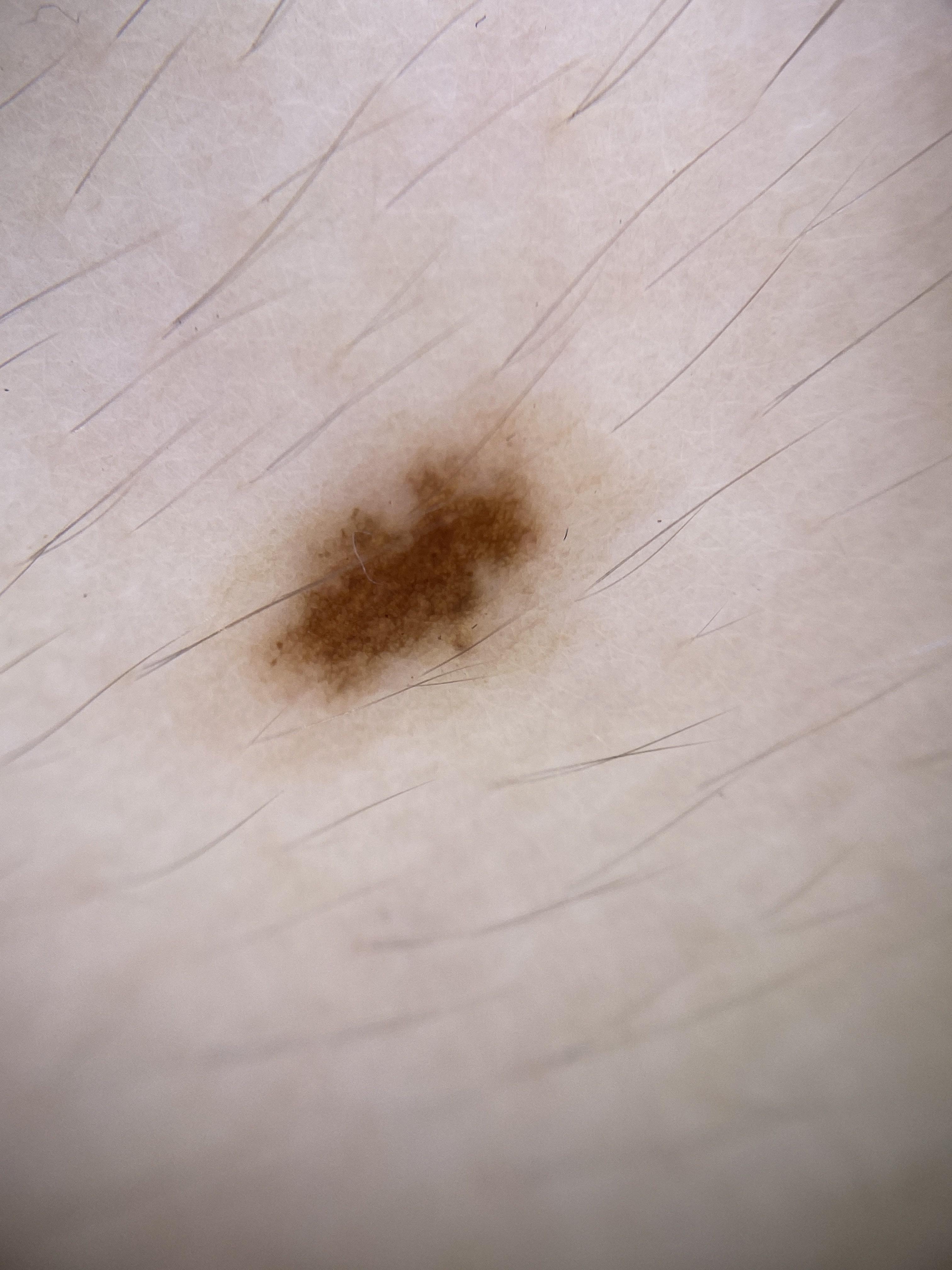Case:
– diagnostic label · Nevus (clinical impression)